The lesion is described as flat · this image was taken at a distance · FST II; human graders estimated a Monk Skin Tone of 2 · self-categorized by the patient as a rash · the subject is 40–49, female · the affected area is the leg.
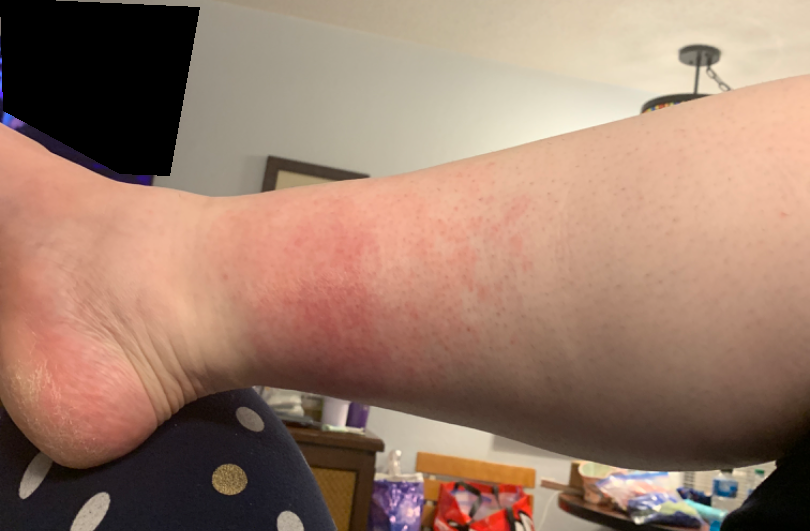Review: In keeping with Stasis Dermatitis.